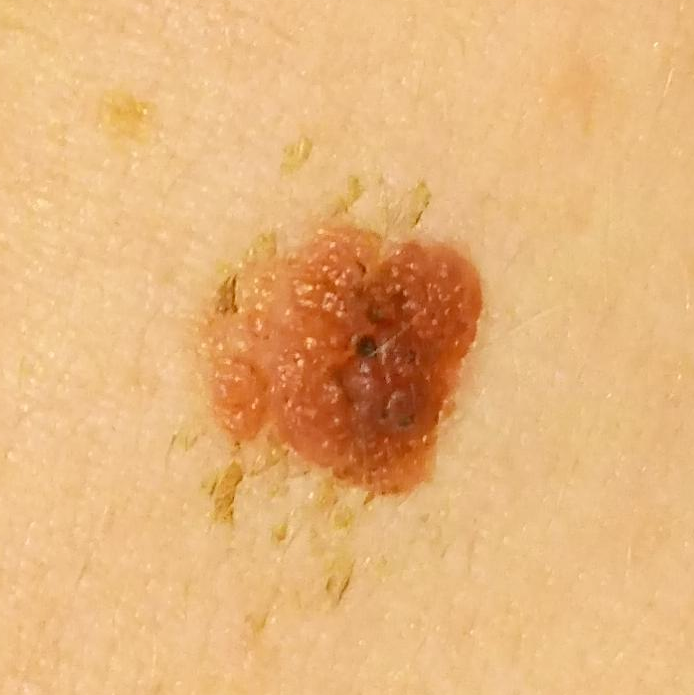image type: smartphone clinical photo | subject: in their 30s | location: the back | patient-reported symptoms: elevation, growth | impression: nevus (clinical consensus).